A dermoscopy image of a skin lesion · the patient says their skin tans without first burning · a female subject 64 years of age · by self-report, a family history of skin cancer, a personal history of cancer, no prior organ transplant, and no personal history of skin cancer · referred with a clinical suspicion of basal cell carcinoma:
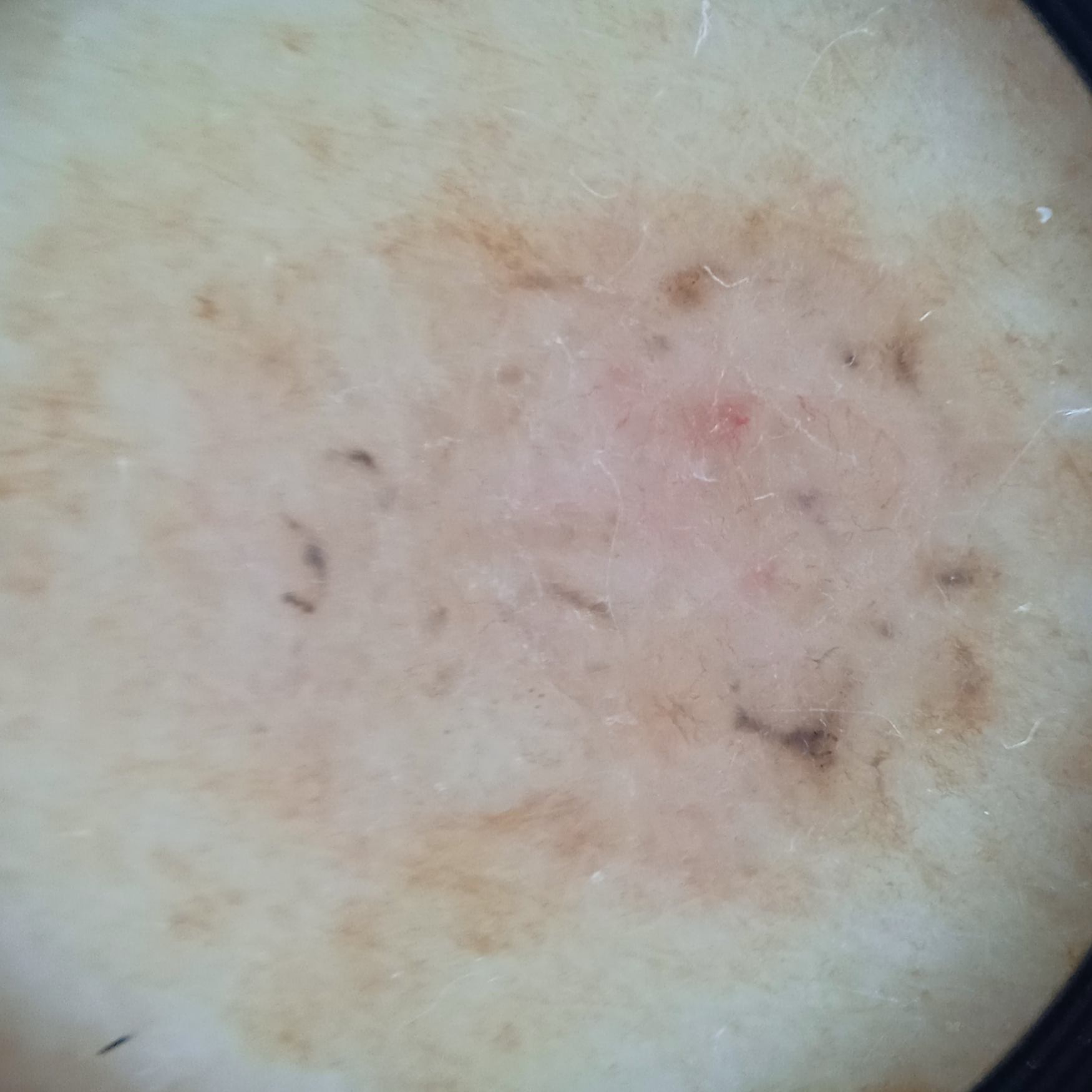Located on the back.
Measuring roughly 9.8 mm.
Histopathologically confirmed as a basal cell carcinoma, following excision, with a measured tumor thickness of 1 mm.